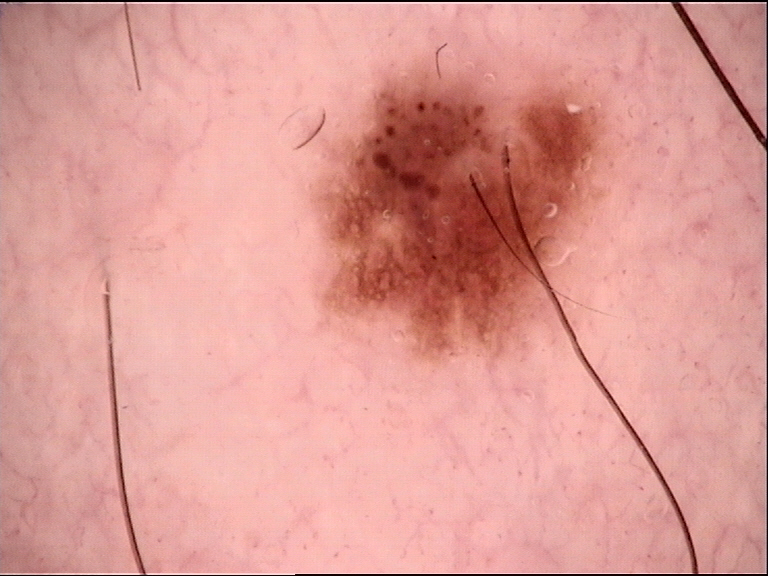diagnostic label: dysplastic junctional nevus (expert consensus).